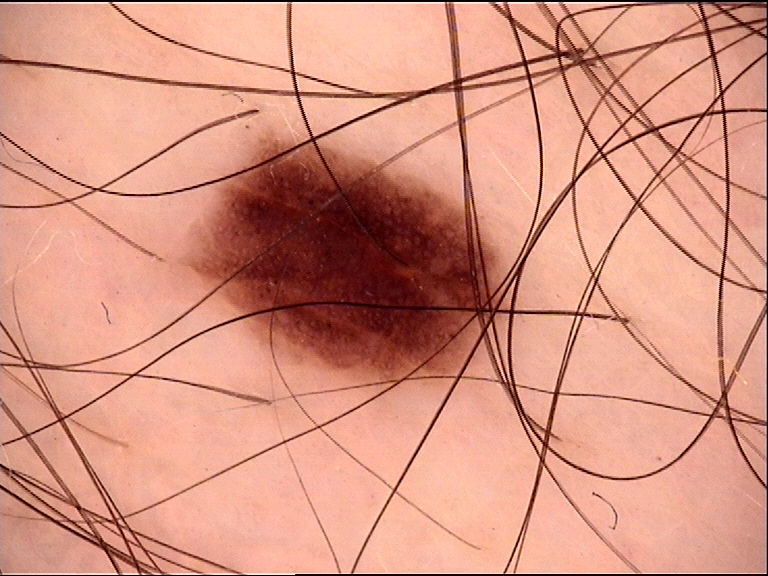| field | value |
|---|---|
| image type | dermatoscopy |
| class | dysplastic junctional nevus (expert consensus) |